The photograph is a close-up of the affected area · located on the leg.
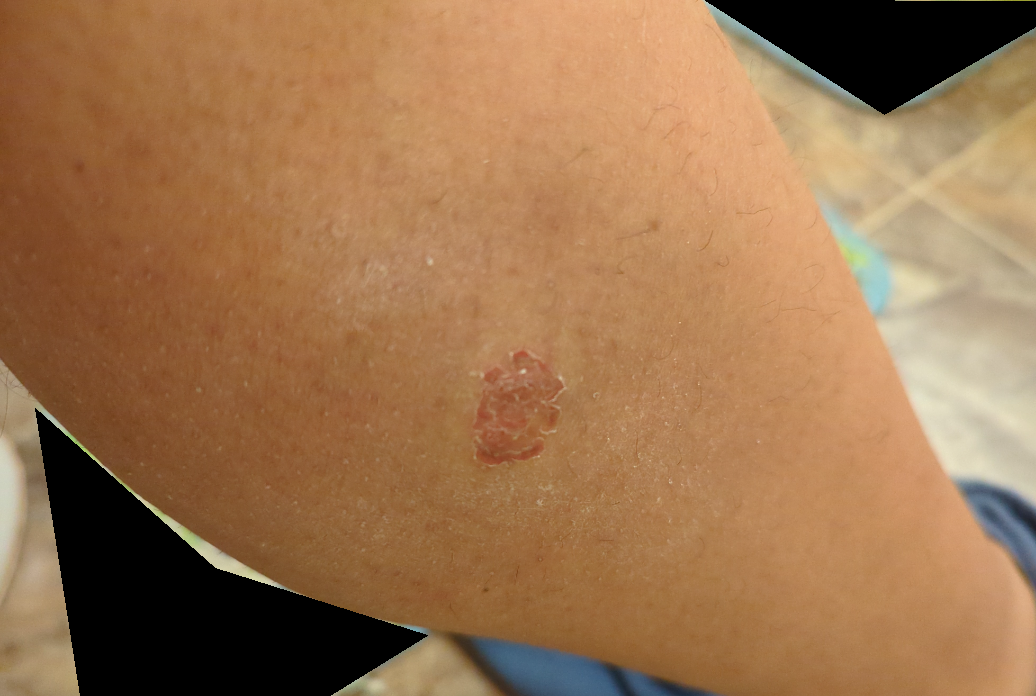Assessment: The case was difficult to assess from the available photograph.